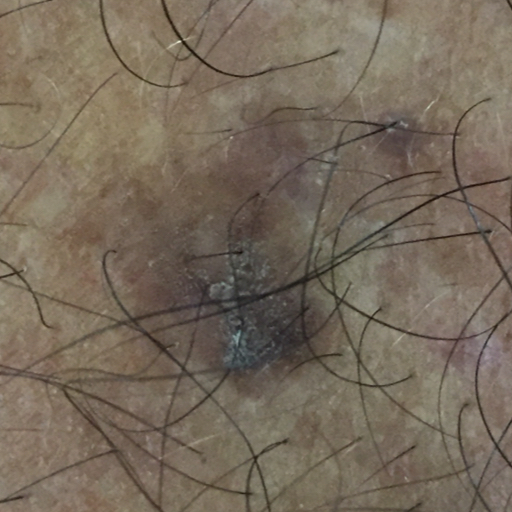A clinical photograph showing a skin lesion. The lesion involves a forearm. The patient describes that the lesion itches. Diagnosed by dermatologist consensus as a seborrheic keratosis.